Dermoscopy of a skin lesion.
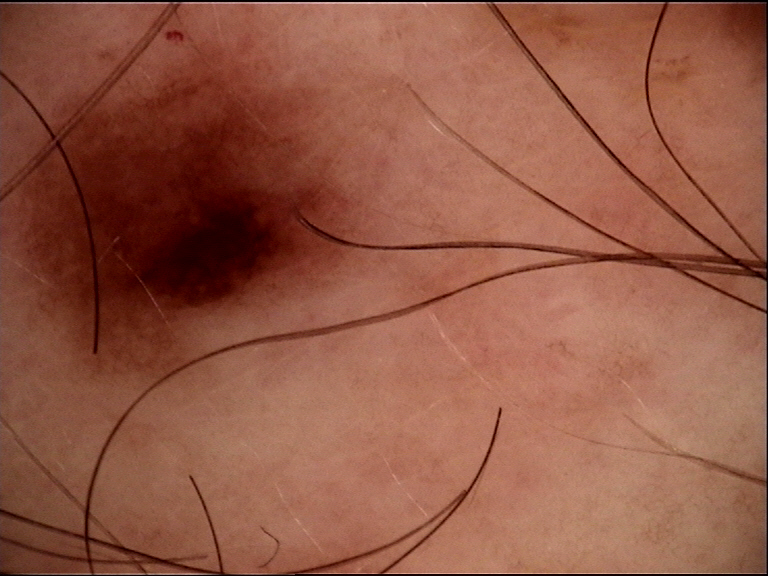Consistent with a benign lesion — a dysplastic junctional nevus.